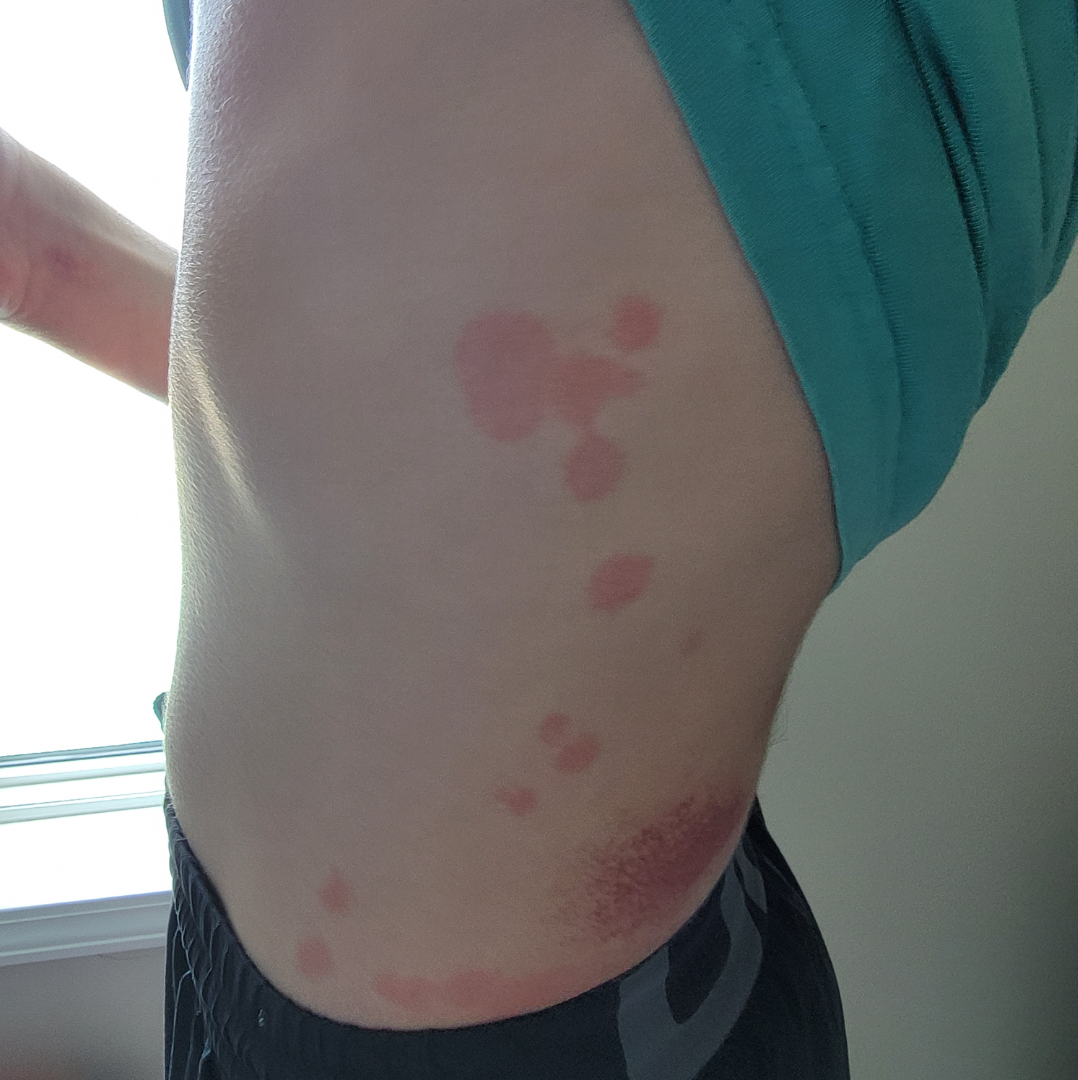shot_type: at a distance
patient: male, age 18–29
body_site:
  - leg
  - back of the hand
  - palm
  - arm
  - head or neck
  - back of the torso
  - front of the torso
systemic_symptoms: none reported
duration: less than one week
skin_tone:
  fitzpatrick: III
symptoms:
  - itching
  - burning
texture:
  - raised or bumpy
  - flat
differential:
  leading:
    - Urticaria